The photo was captured at a distance, located on the arm: 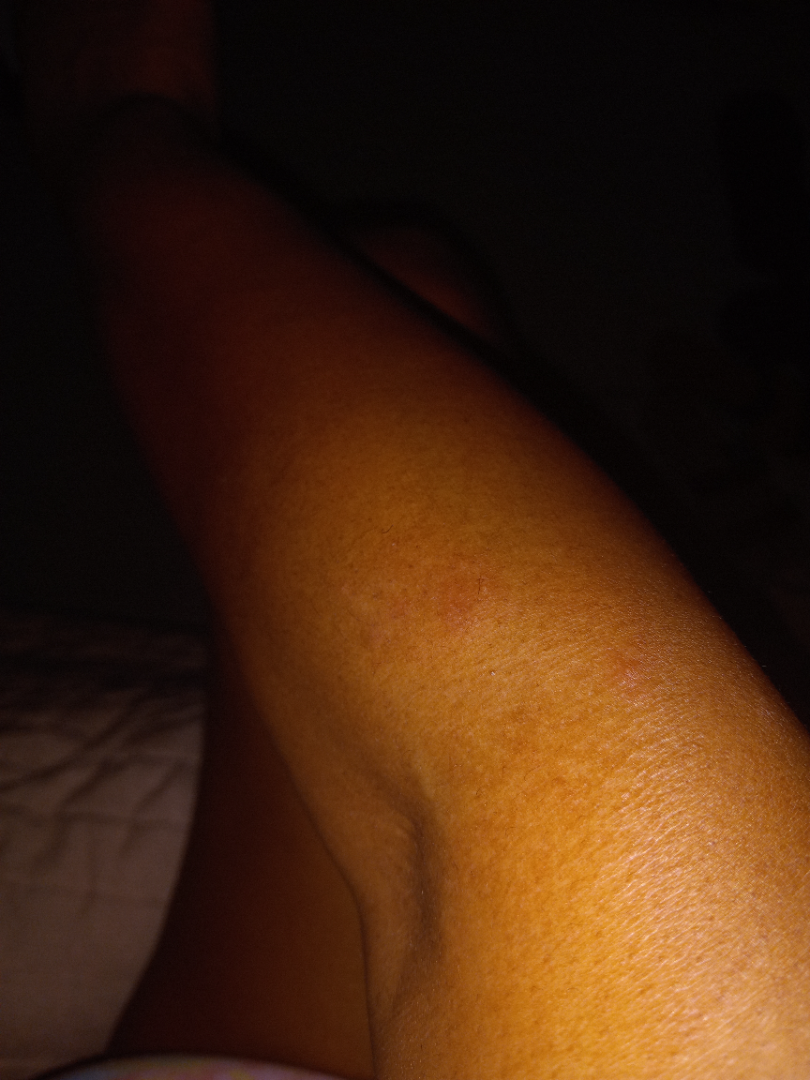Case summary:
– differential · one reviewing dermatologist: the leading consideration is Eczema; also raised was Psoriasis